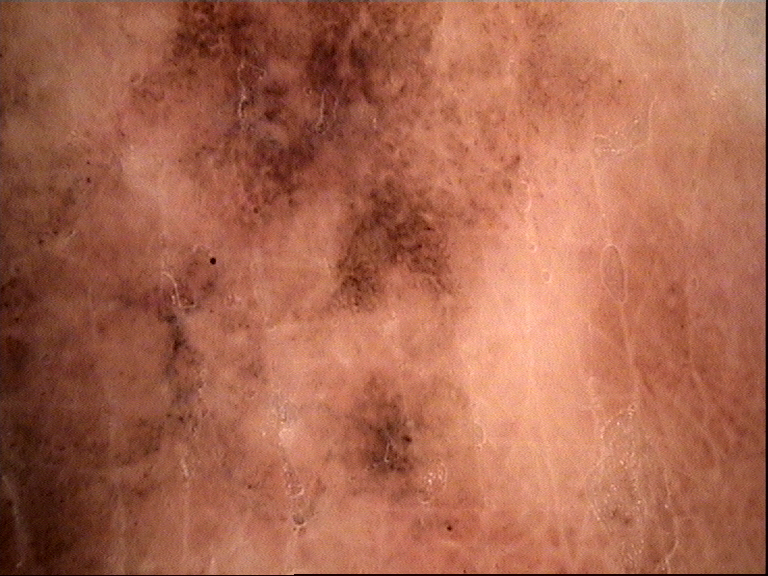Biopsy-confirmed as an acral lentiginous melanoma.